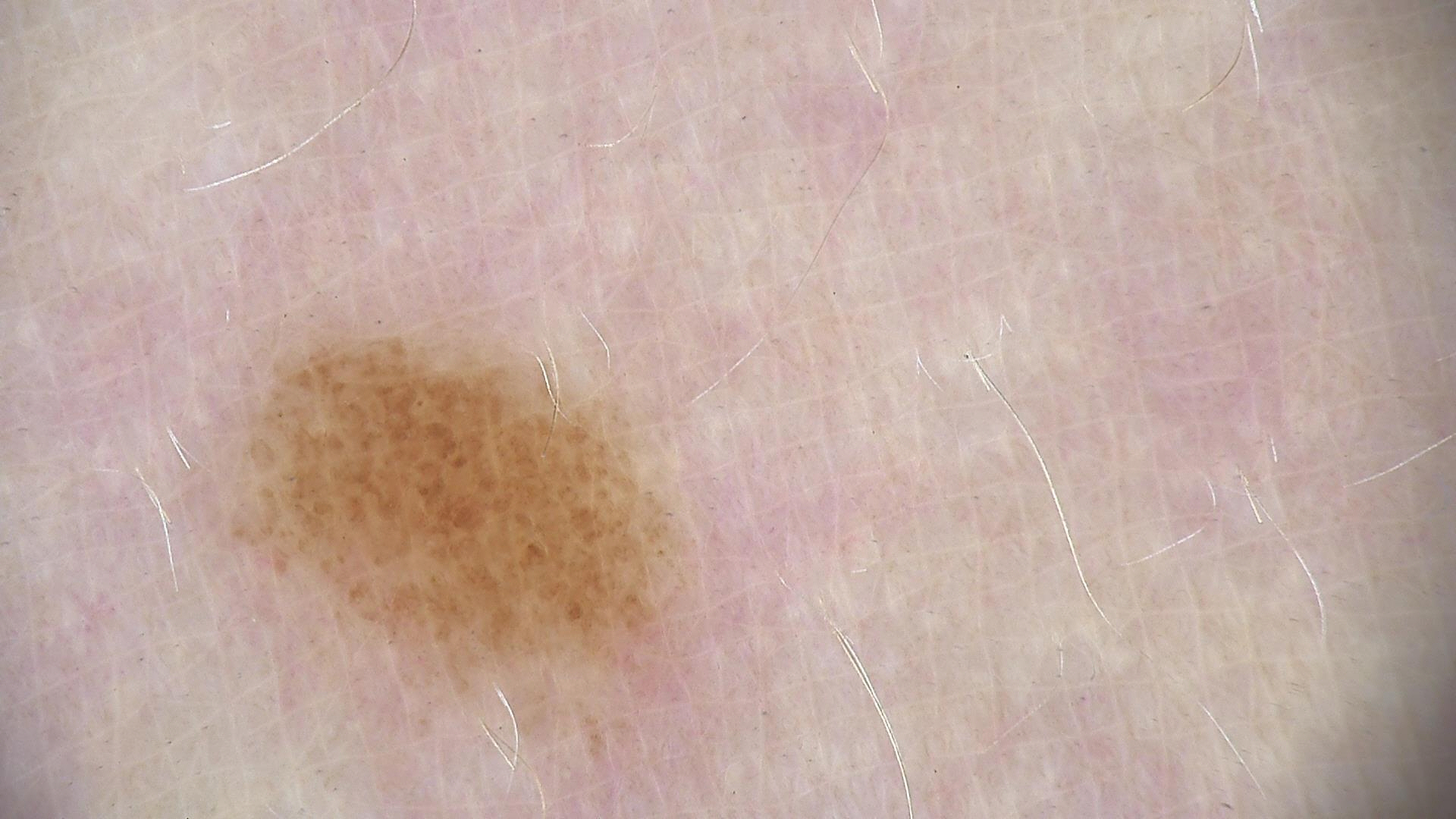A dermatoscopic image of a skin lesion. Labeled as a dysplastic junctional nevus.